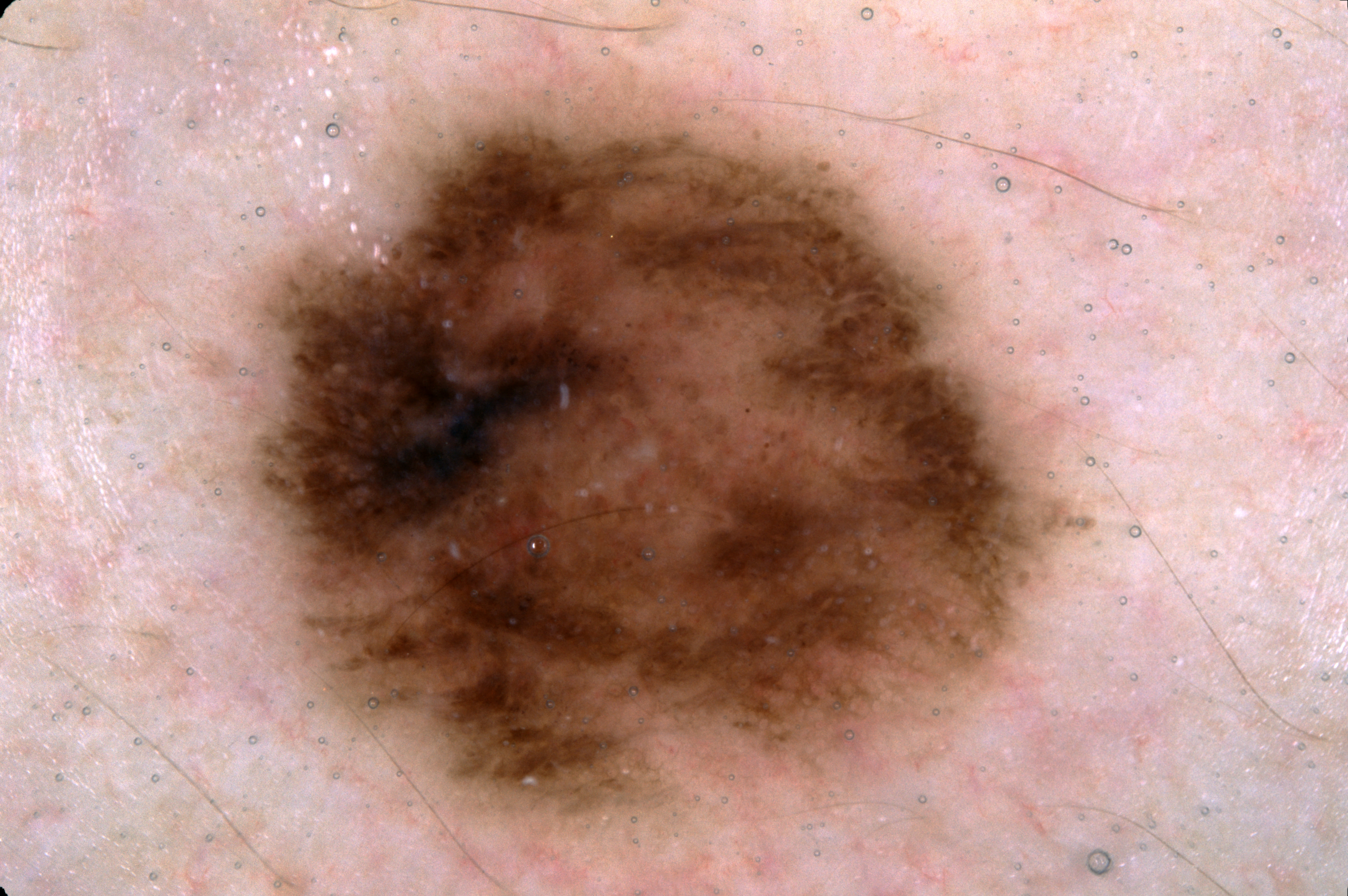Image and clinical context: The subject is female. Dermoscopy of a skin lesion. The lesion is located at 237, 89, 1080, 841. The lesion takes up about 36% of the image. Dermoscopic assessment notes pigment network. Impression: The diagnostic assessment was a melanocytic nevus, a benign lesion.